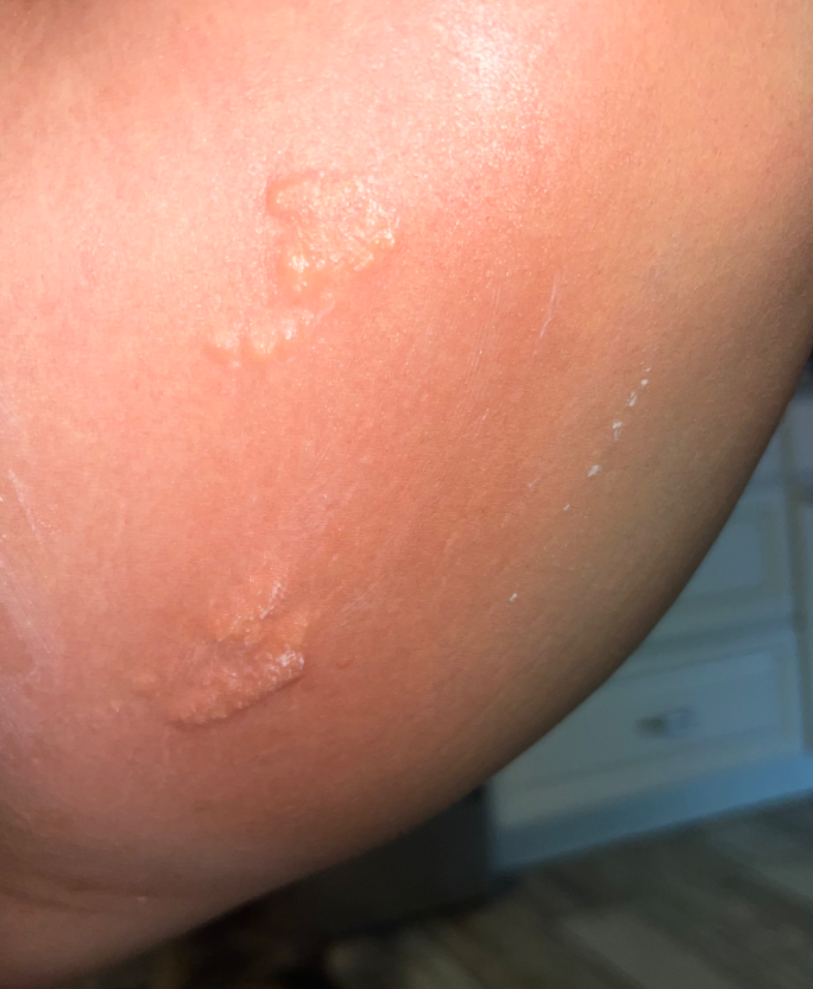assessment: unable to determine
patient: female, age 18–29
shot_type: close-up
body_site:
  - front of the torso
  - leg
  - head or neck